An image taken at a distance. The subject is a female aged 30–39:
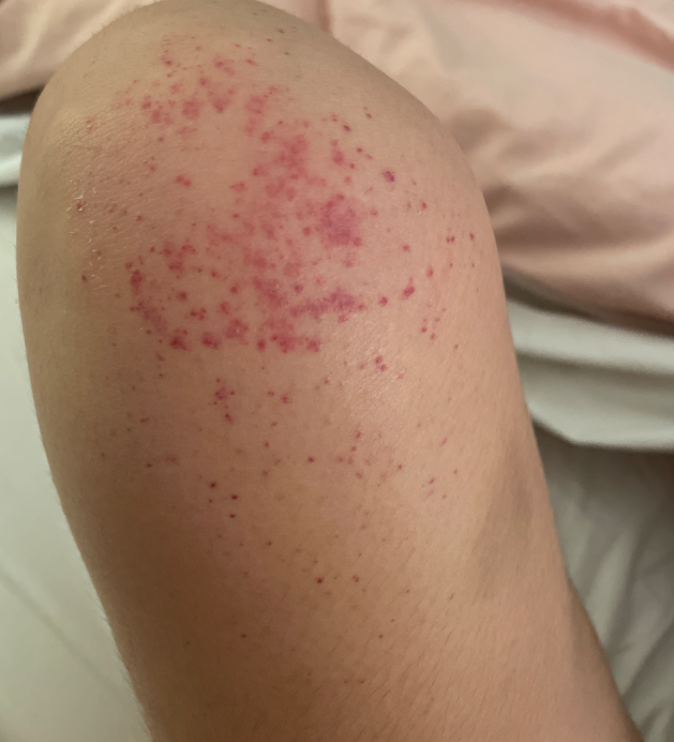assessment: indeterminate